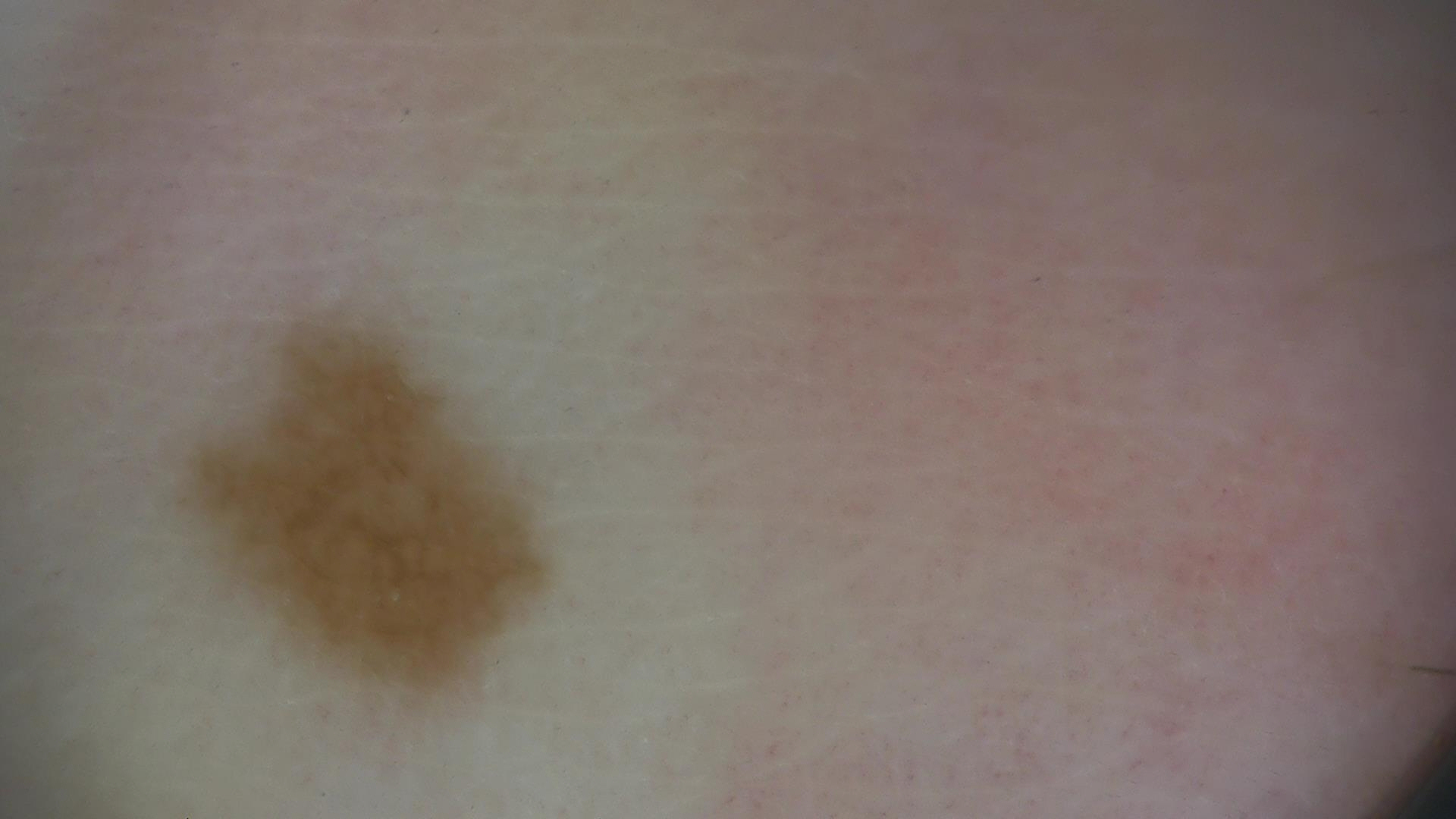image: dermoscopy
diagnosis:
  name: dysplastic junctional nevus
  code: jd
  malignancy: benign
  super_class: melanocytic
  confirmation: expert consensus